A dermoscopic image of a skin lesion.
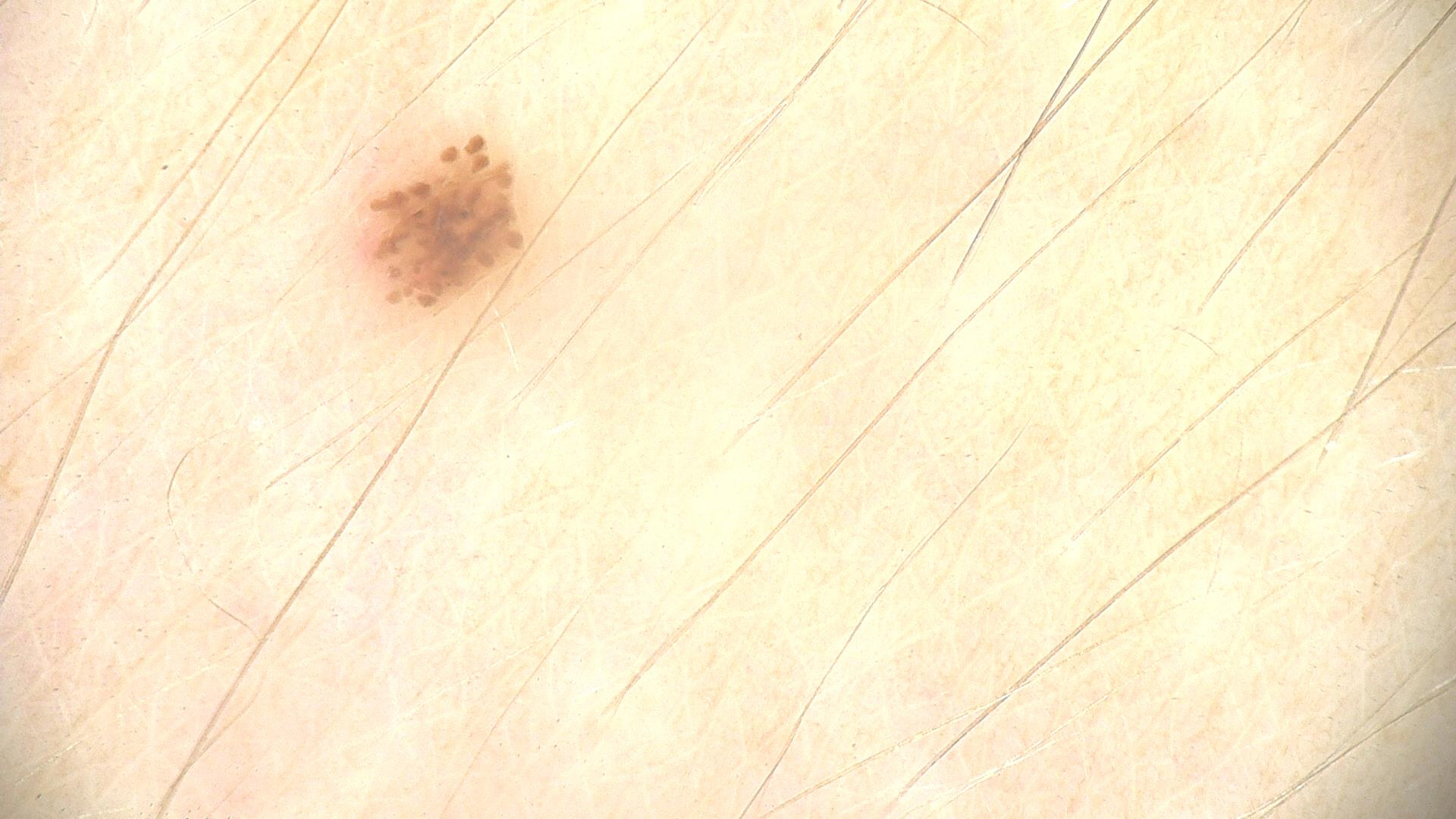| feature | finding |
|---|---|
| class | dysplastic junctional nevus (expert consensus) |